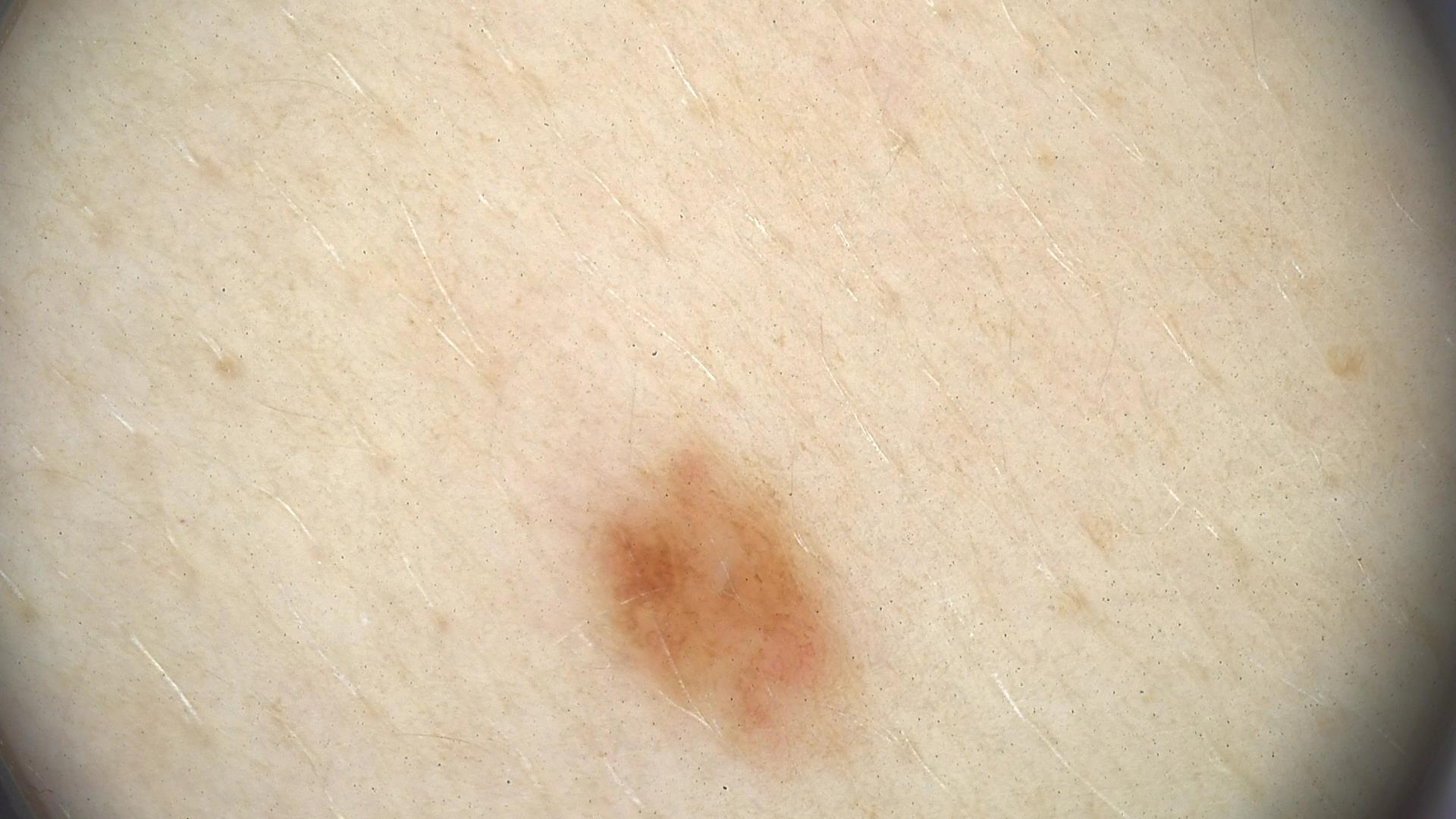Labeled as a benign lesion — a dysplastic junctional nevus.